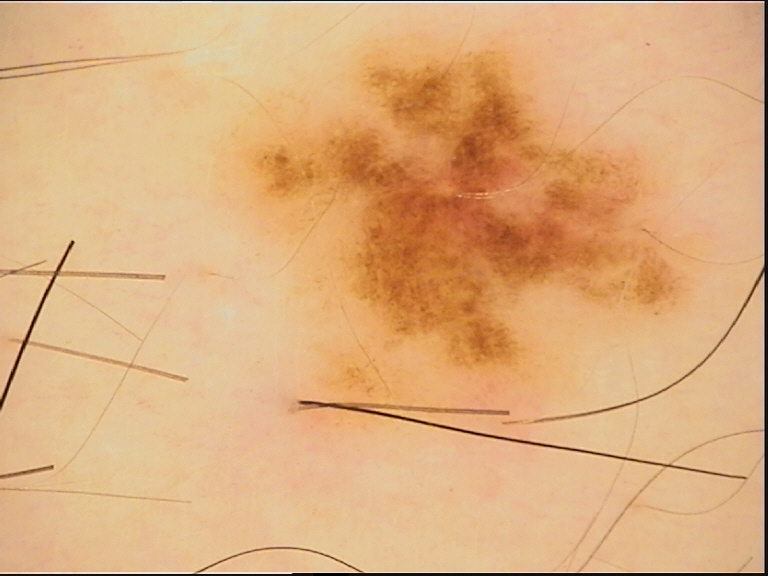The diagnosis was a dysplastic junctional nevus.